A close-up photograph.
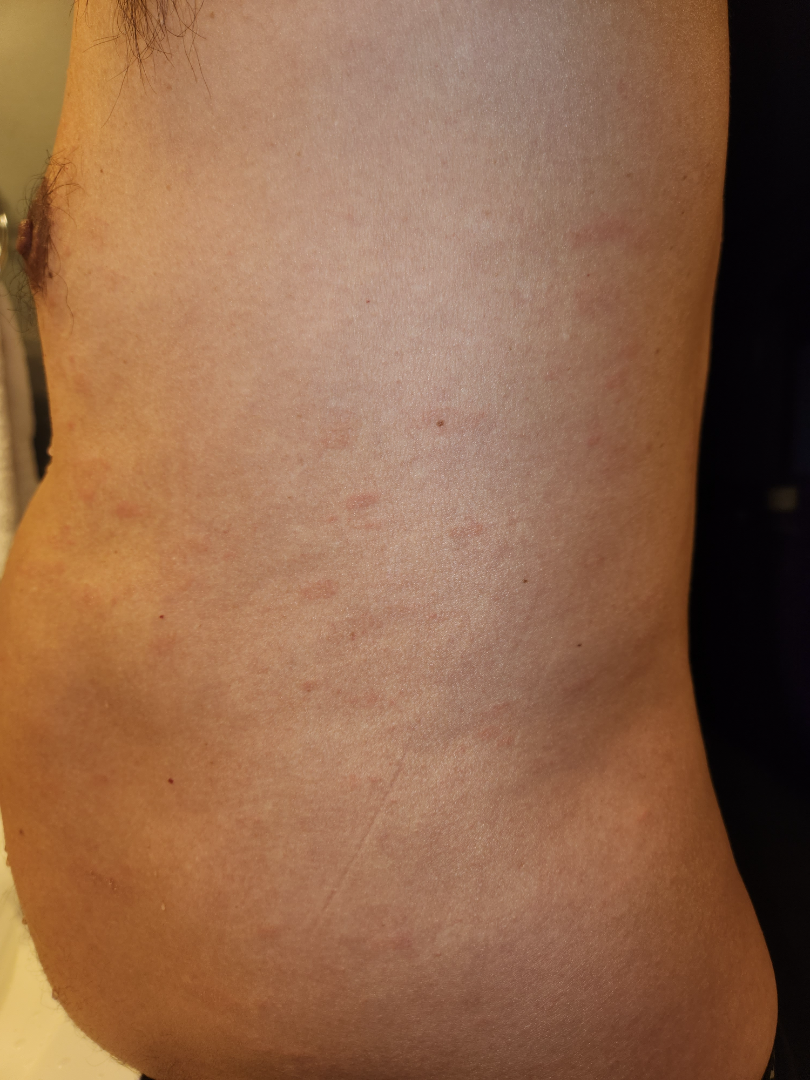On dermatologist assessment of the image, the leading consideration is Pityriasis rosea; the differential also includes Syphilis.